The chart records a previous melanoma; recorded as Fitzpatrick skin type II; a clinical photograph of a skin lesion.
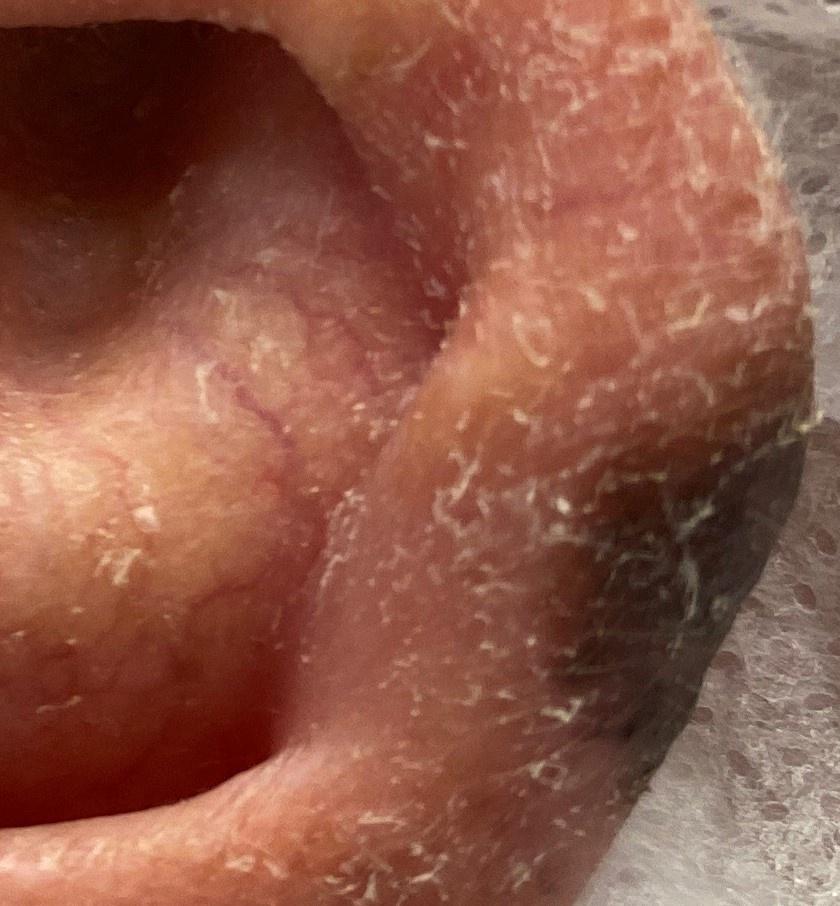The lesion involves the head or neck. The biopsy diagnosis was a skin cancer — a melanoma.